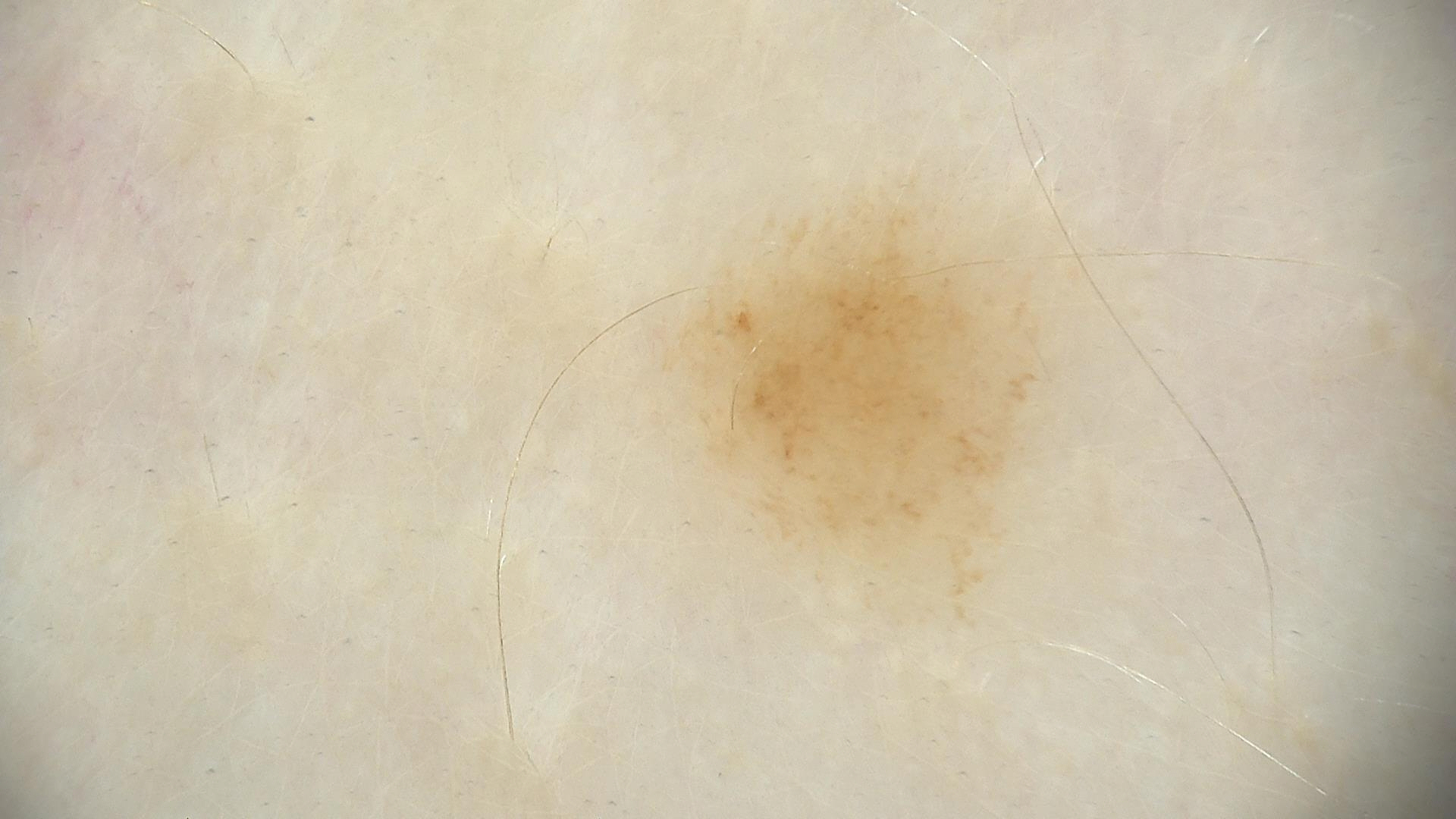Summary:
A dermoscopic image of a skin lesion.
Conclusion:
Labeled as a dysplastic junctional nevus.